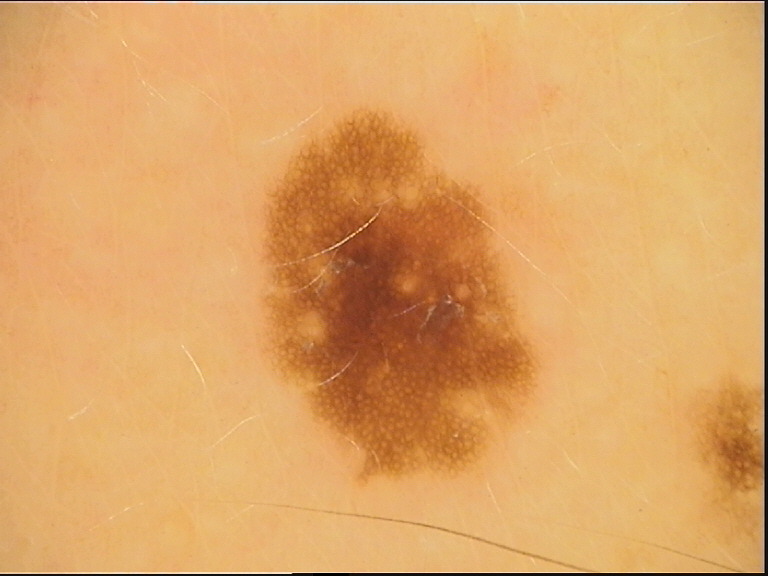diagnostic label = dysplastic junctional nevus (expert consensus).